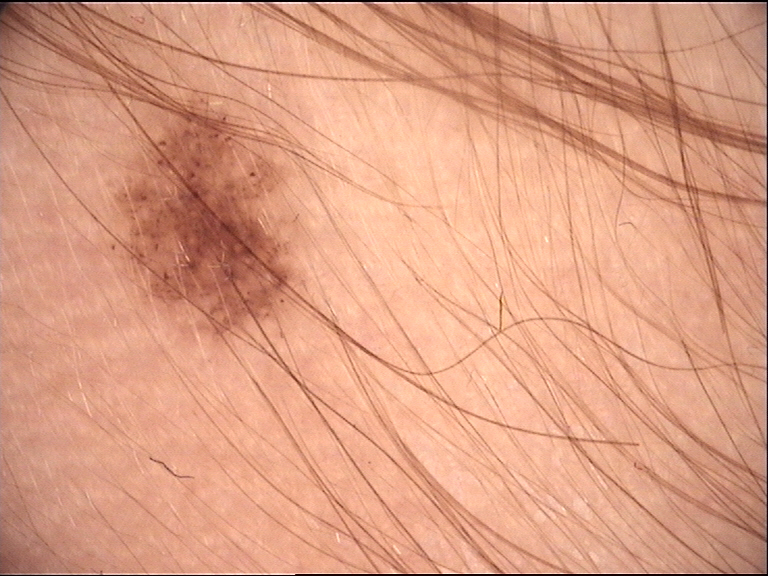| feature | finding |
|---|---|
| assessment | congenital junctional nevus (expert consensus) |